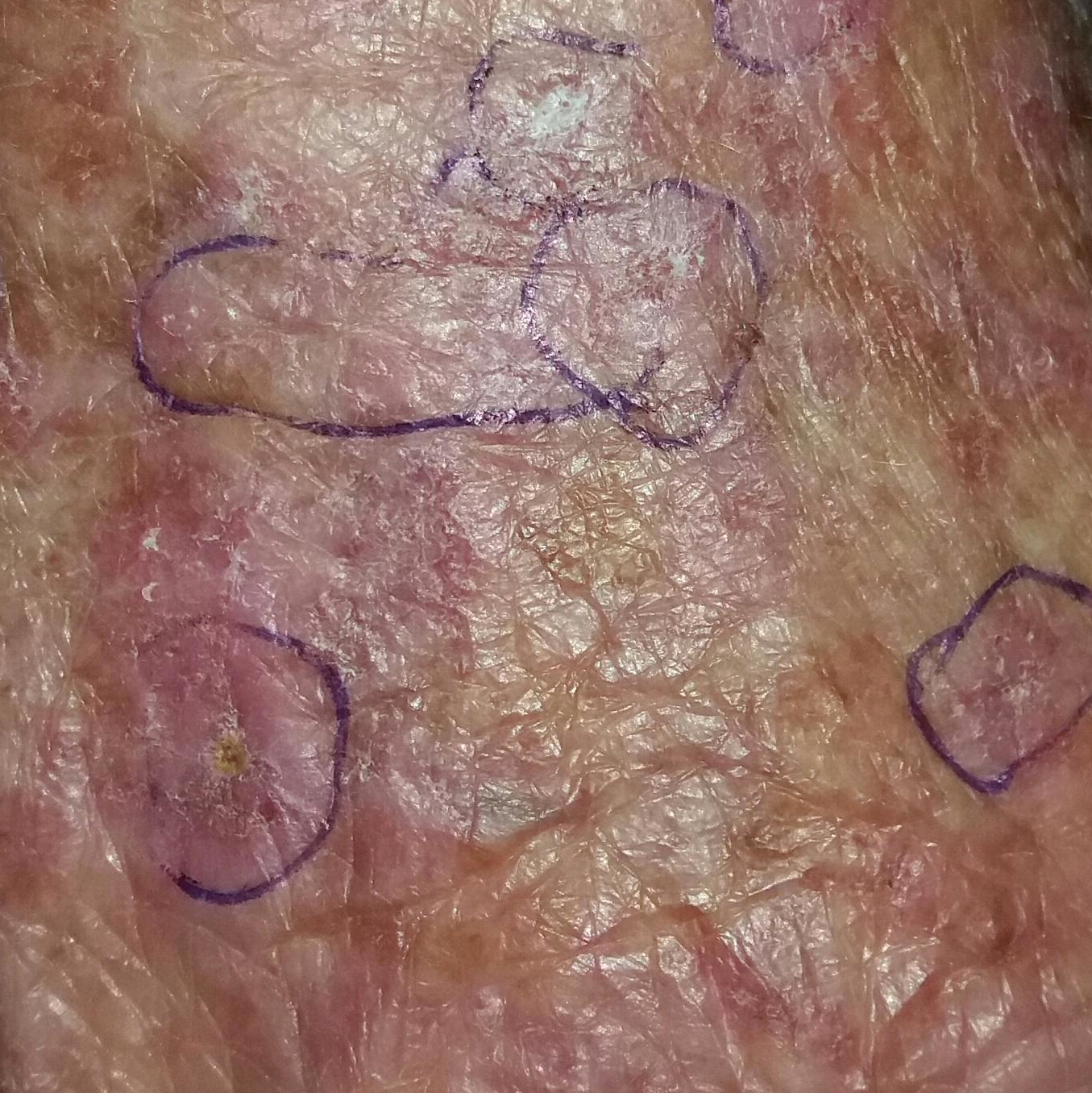A patient aged 52. A clinical close-up photograph of a skin lesion. The patient describes that the lesion itches. The consensus clinical diagnosis was an actinic keratosis.